The photo was captured at a distance.
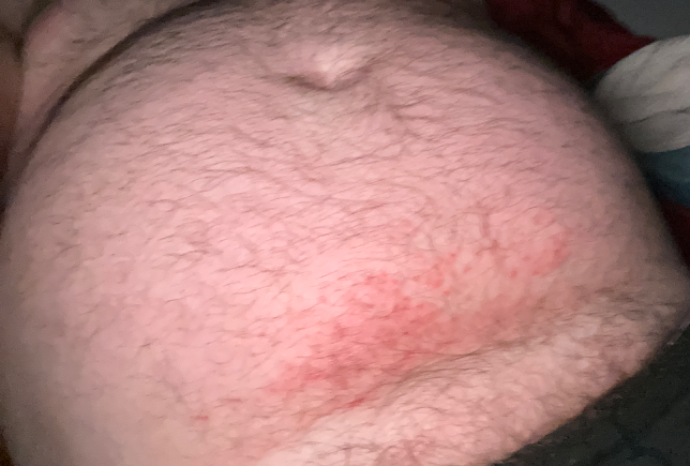Reported duration is one to four weeks. Reported lesion symptoms include bothersome appearance, itching and enlargement. The patient indicates the lesion is raised or bumpy. On teledermatology review, Intertrigo (possible); Eczema (possible); Allergic Contact Dermatitis (lower probability).